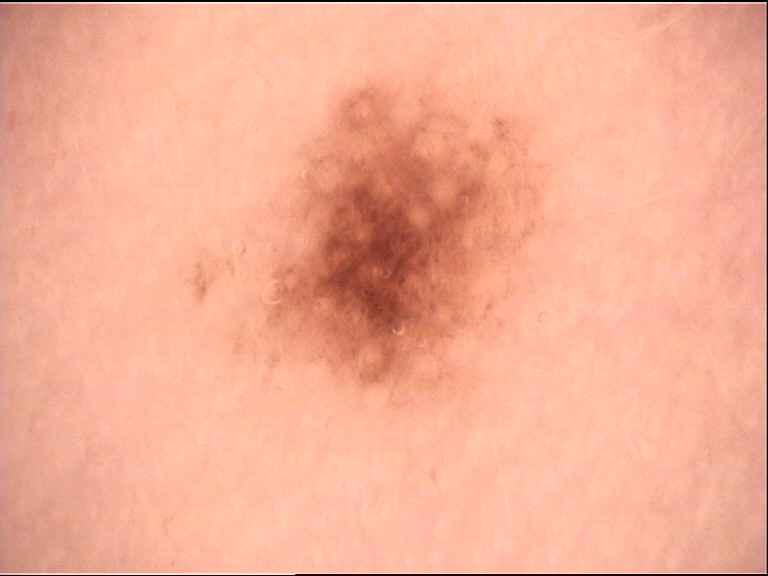Findings: The morphology is that of a banal lesion. Conclusion: Diagnosed as a compound nevus.